A dermatoscopic image of a skin lesion:
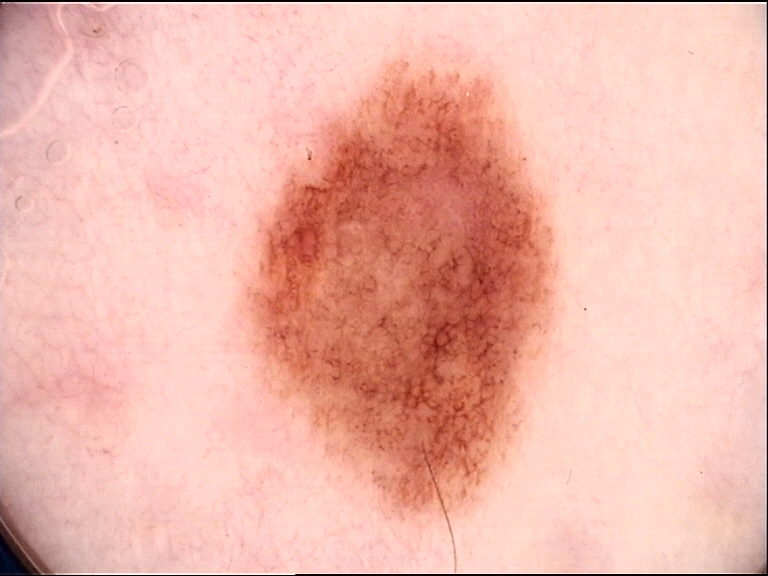The diagnosis was a dysplastic junctional nevus.